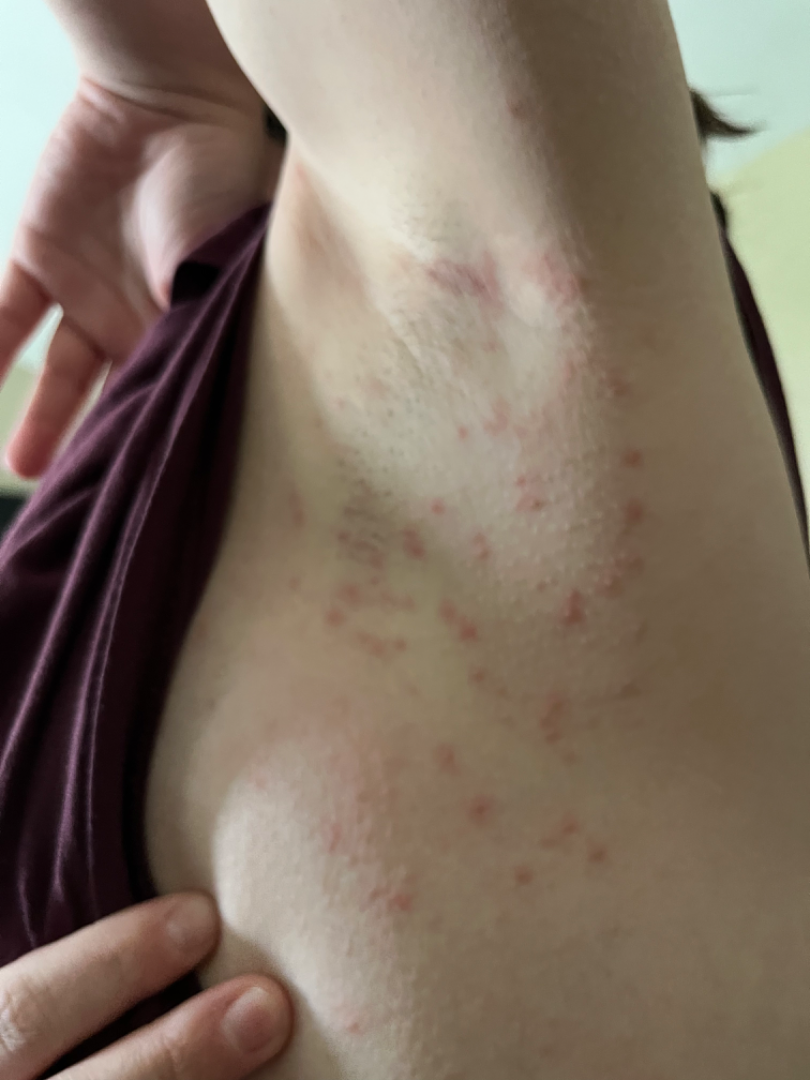The reviewer was unable to grade this case for skin condition. The lesion is described as raised or bumpy. Present for less than one week. The lesion is associated with itching, pain, burning and bothersome appearance. The arm is involved. An image taken at a distance. The patient considered this acne.